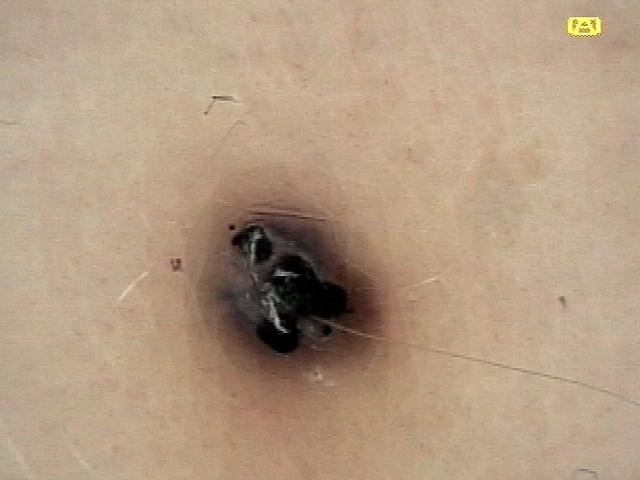A skin lesion imaged with a dermatoscope. A male patient aged 68 to 72. The lesion involves the trunk. The clinical impression was a vascular lesion.